Located on the leg · the photograph is a close-up of the affected area: 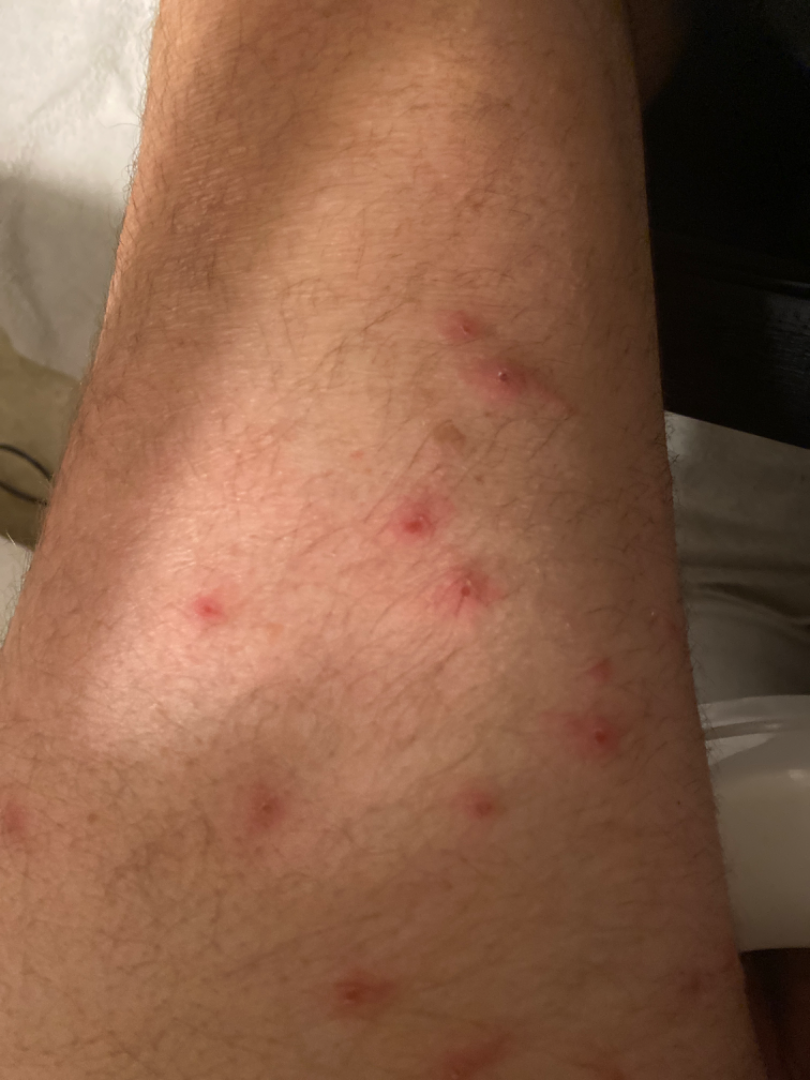Impression: On photographic review: the favored diagnosis is Insect Bite; an alternative is Folliculitis.